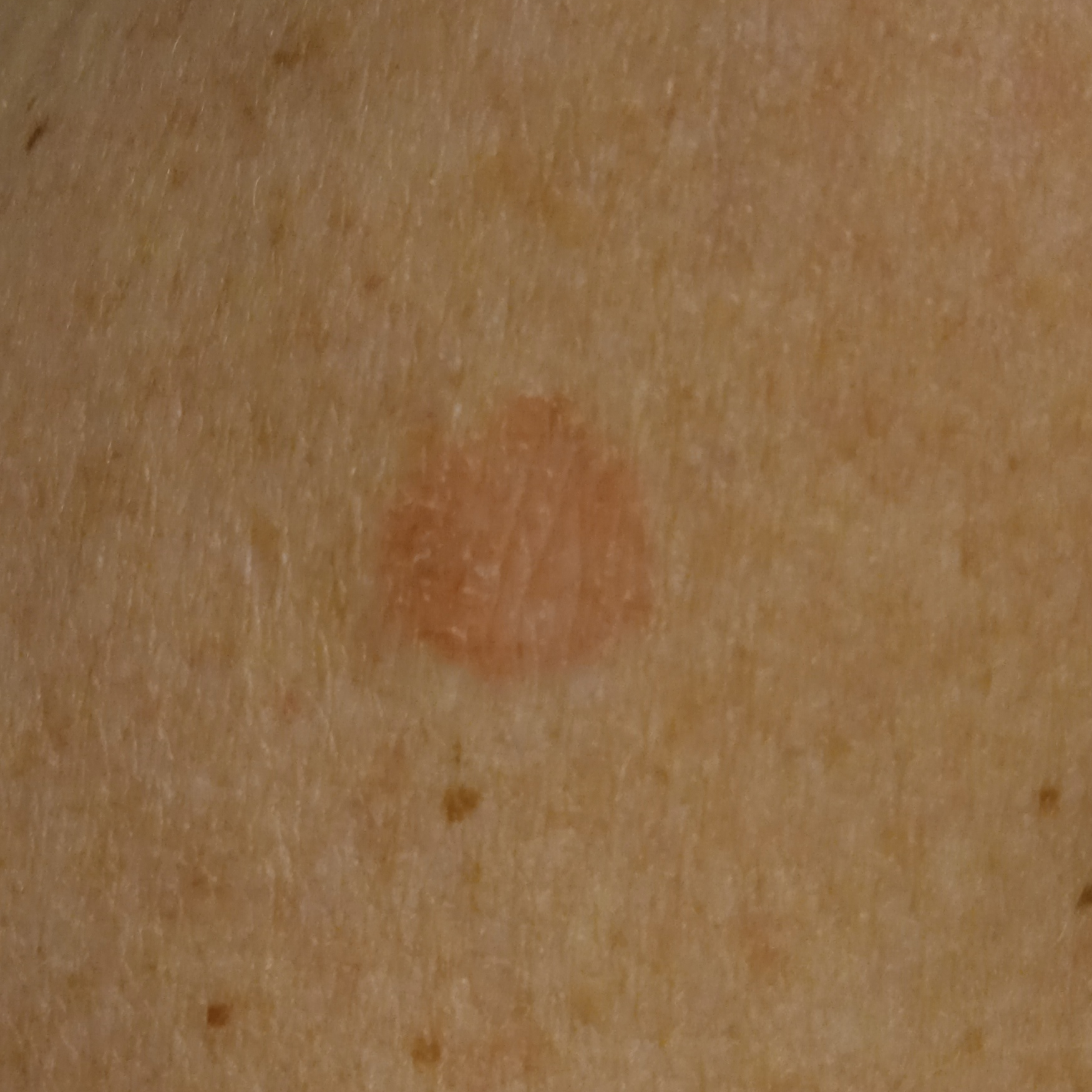Summary:
A clinical photograph of a skin lesion. On a questionnaire the patient reported immunosuppression and a prior organ transplant. A female subject age 55. The patient says their skin reddens painfully with sun exposure. Acquired for a research image collection, with no referral diagnosis. The lesion is on an arm. The lesion is about 13.2 mm across.
Conclusion:
The dermatologists' assessment was a basal cell carcinoma.